Male patient, age 60–69; present for one to four weeks; the arm is involved; the lesion is described as rough or flaky, raised or bumpy and fluid-filled; associated systemic symptoms include joint pain; this is a close-up image; symptoms reported: enlargement, pain, bothersome appearance and burning:
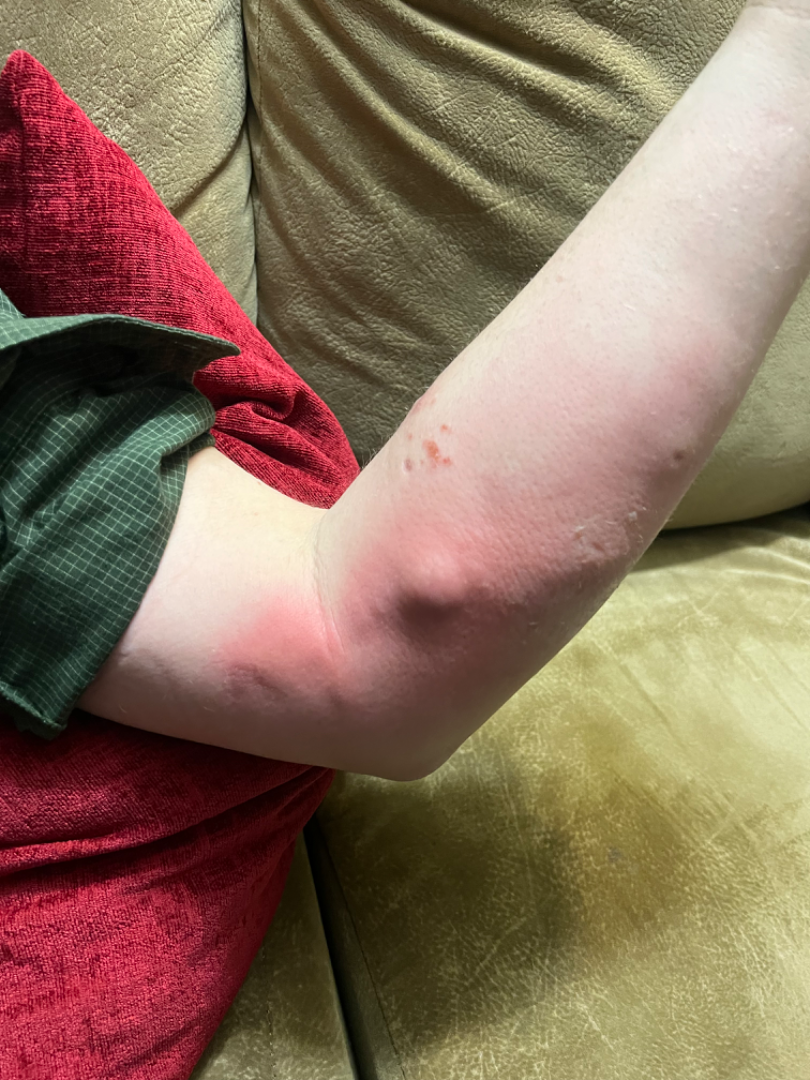| key | value |
|---|---|
| dermatologist impression | reviewed remotely by three dermatologists: the leading consideration is Abscess; possibly Cellulitis; lower on the differential is Localised skin eruption due to drugs and medicaments; less probable is Lymphocutaneous sporotrichosis; less likely is Cutaneous leishmaniasis |